A dermoscopic photograph of a skin lesion: 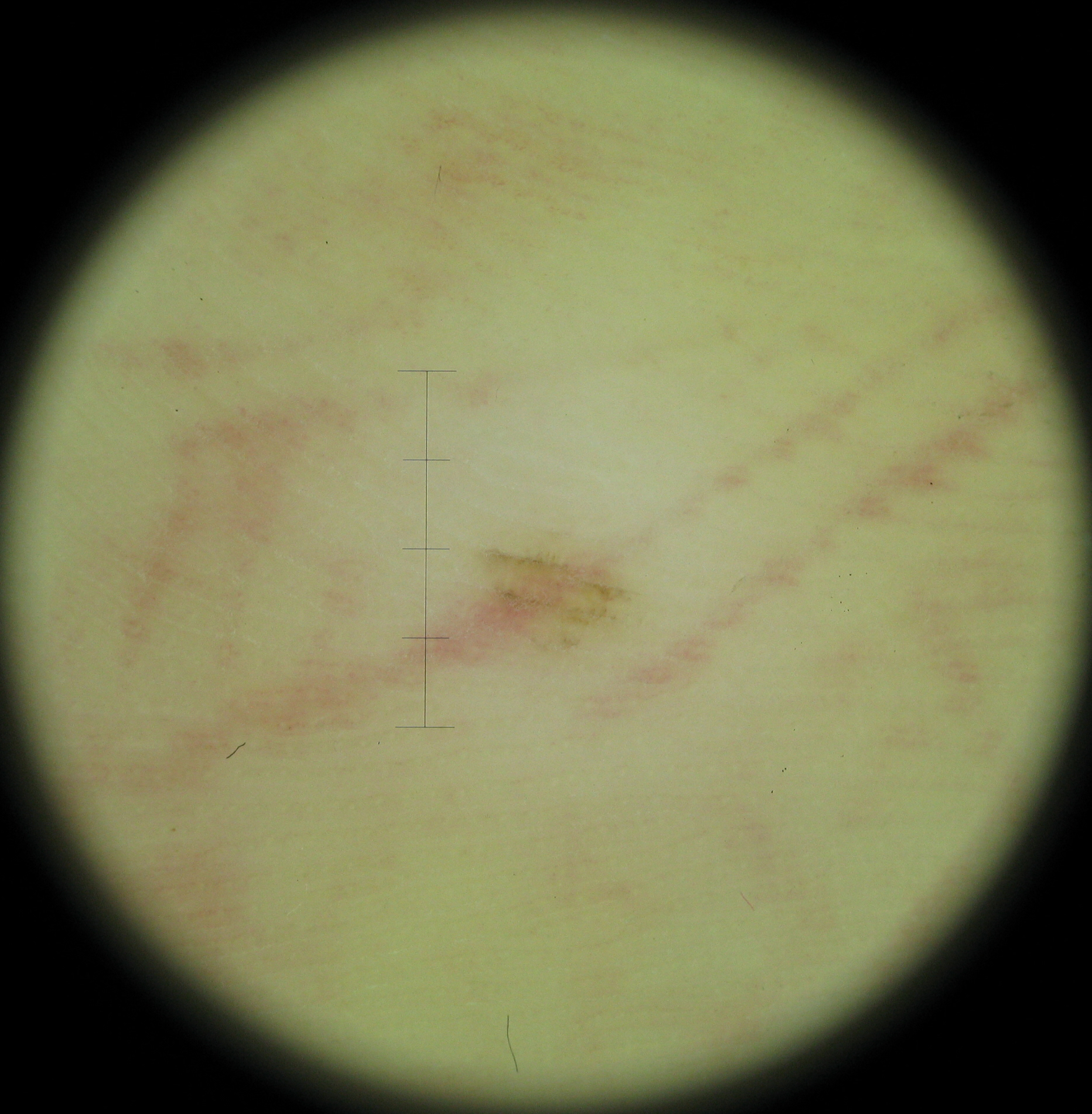Q: What is the lesion category?
A: banal
Q: What is this lesion?
A: acral junctional nevus (expert consensus)